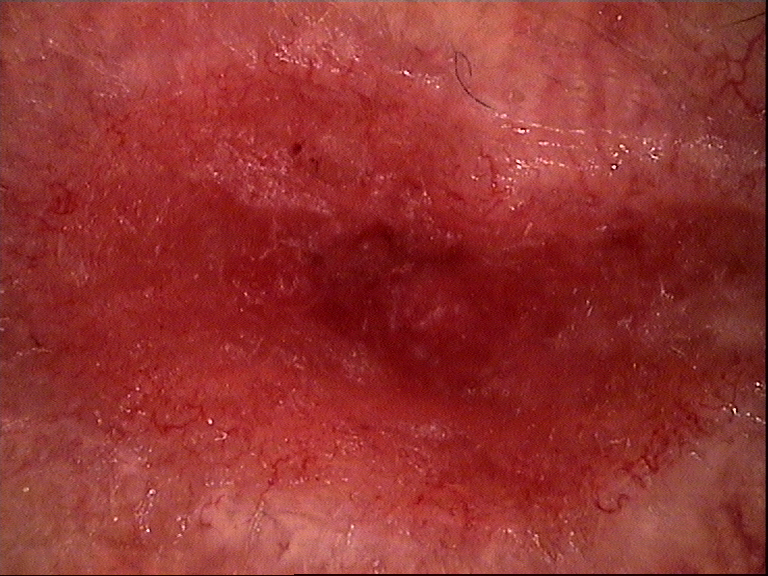A dermoscopy image of a single skin lesion. Biopsy-confirmed as a keratinocytic, malignant lesion — a squamous cell carcinoma.